A dermoscopy image of a single skin lesion.
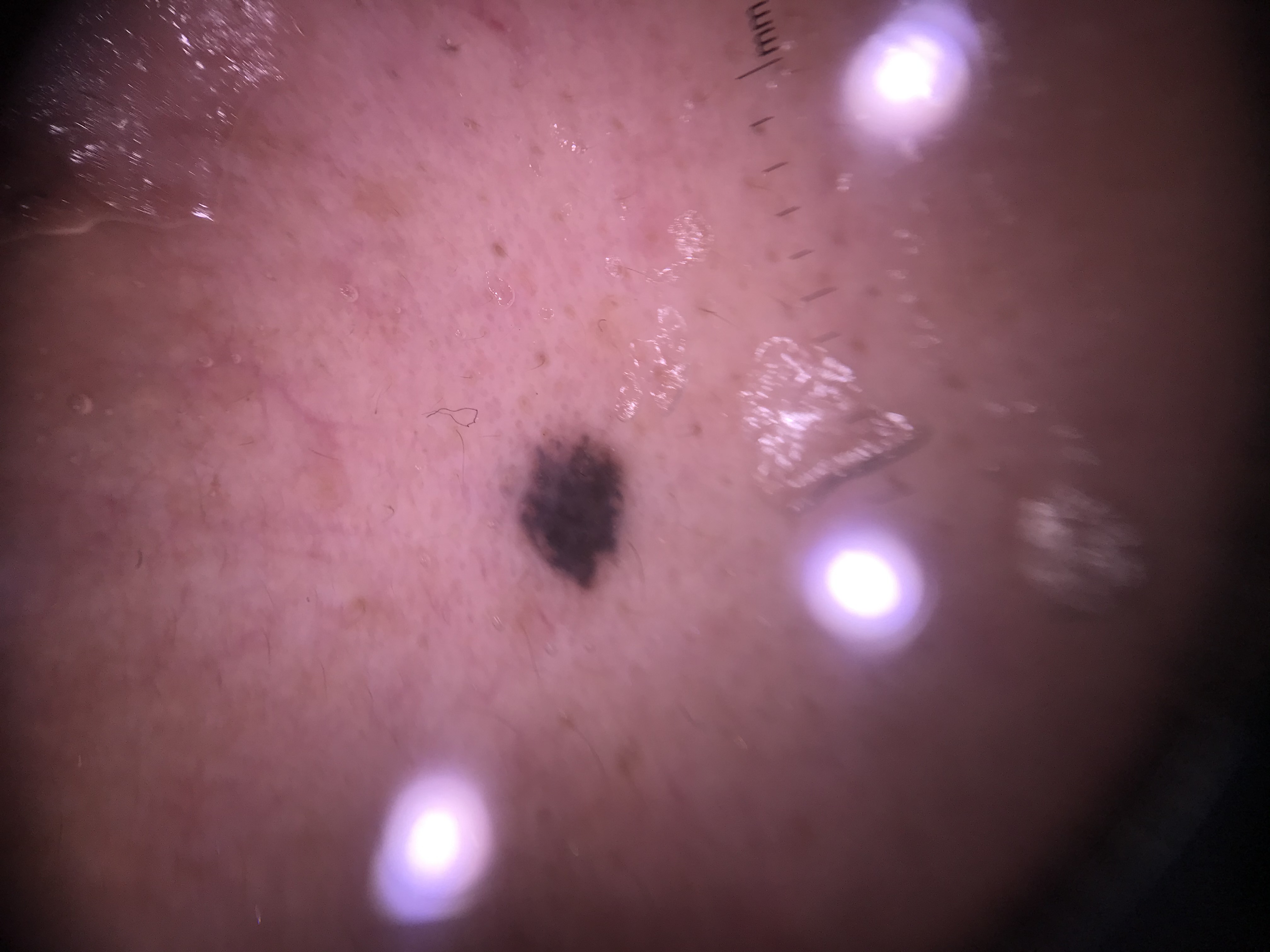Labeled as a banal lesion — a blue nevus.